A dermoscopy image of a single skin lesion.
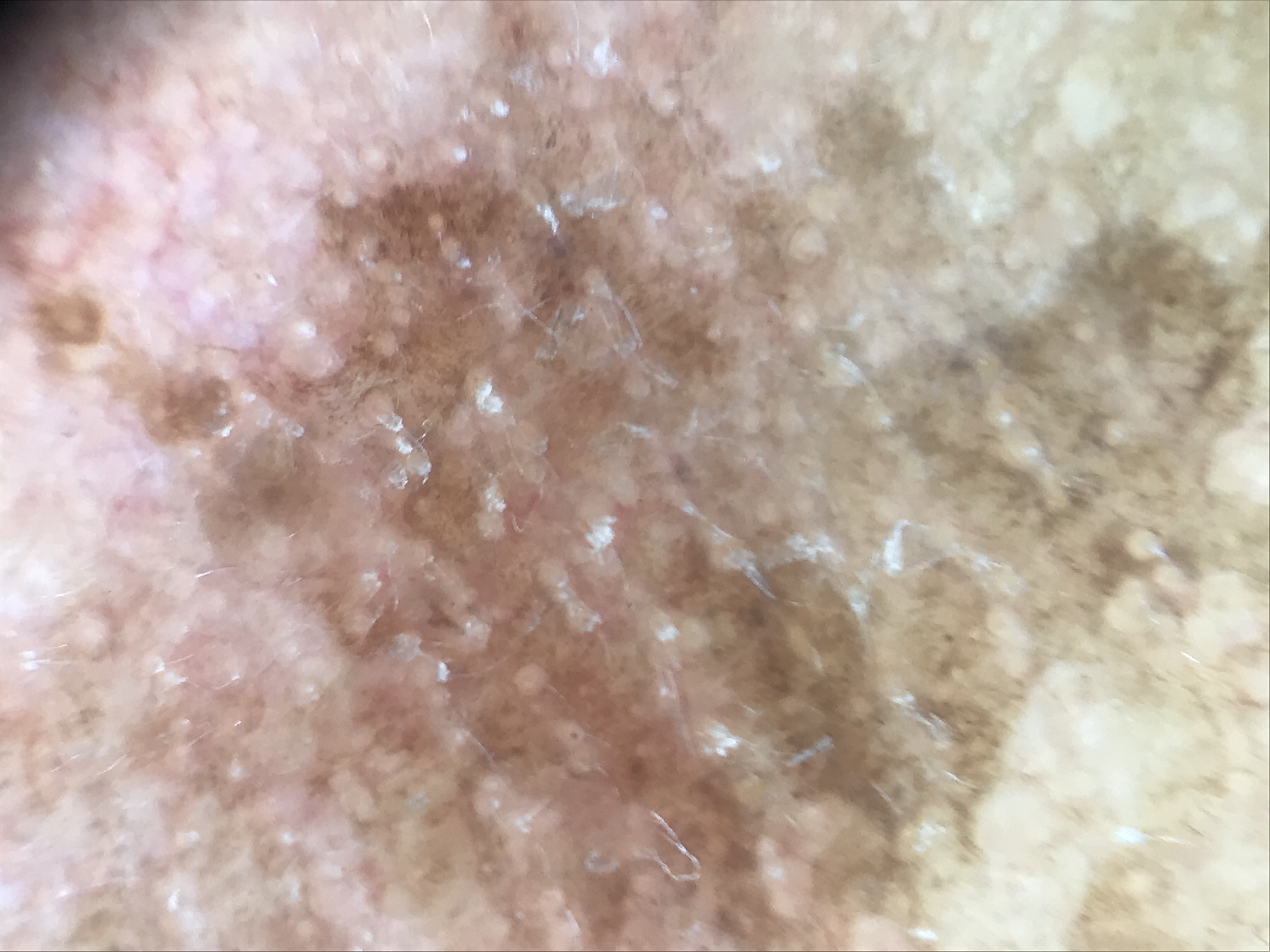Labeled as a keratinocytic lesion — an actinic keratosis.